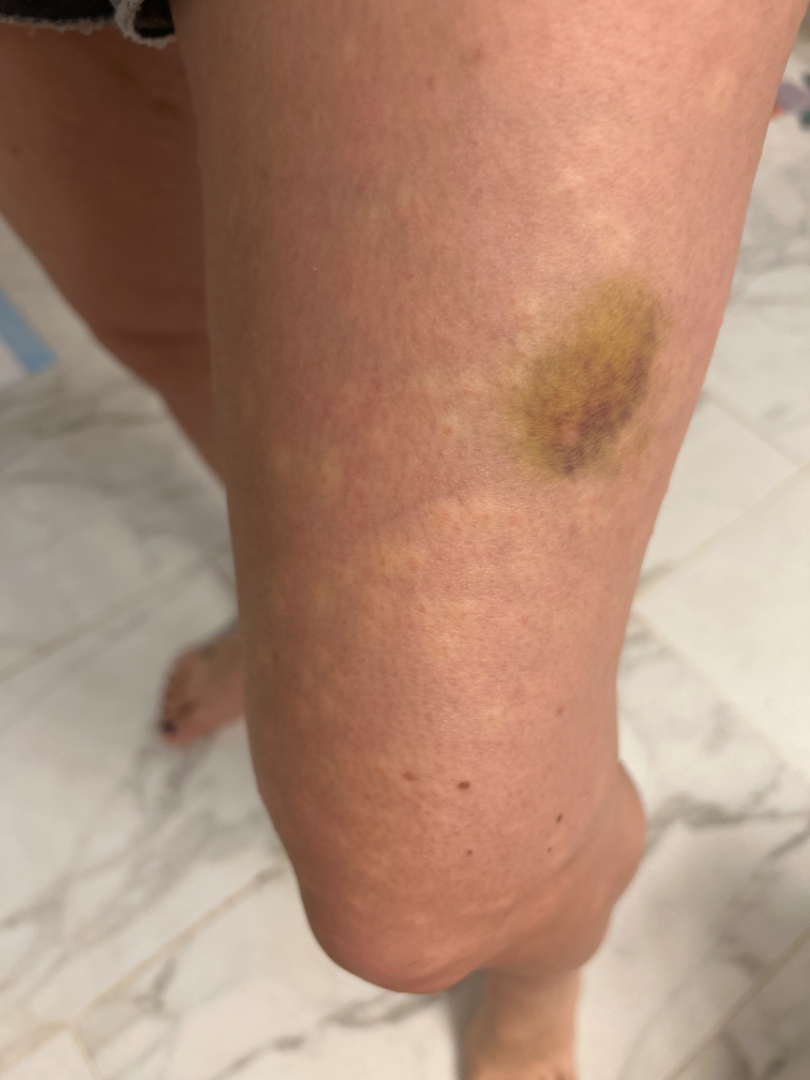{
  "assessment": "indeterminate from the photograph",
  "shot_type": "at an angle",
  "body_site": "leg",
  "symptoms": "itching",
  "patient_category": "a rash",
  "systemic_symptoms": "fatigue",
  "duration": "less than one week",
  "texture": "raised or bumpy"
}